The lesion involves the head or neck; this is a close-up image.
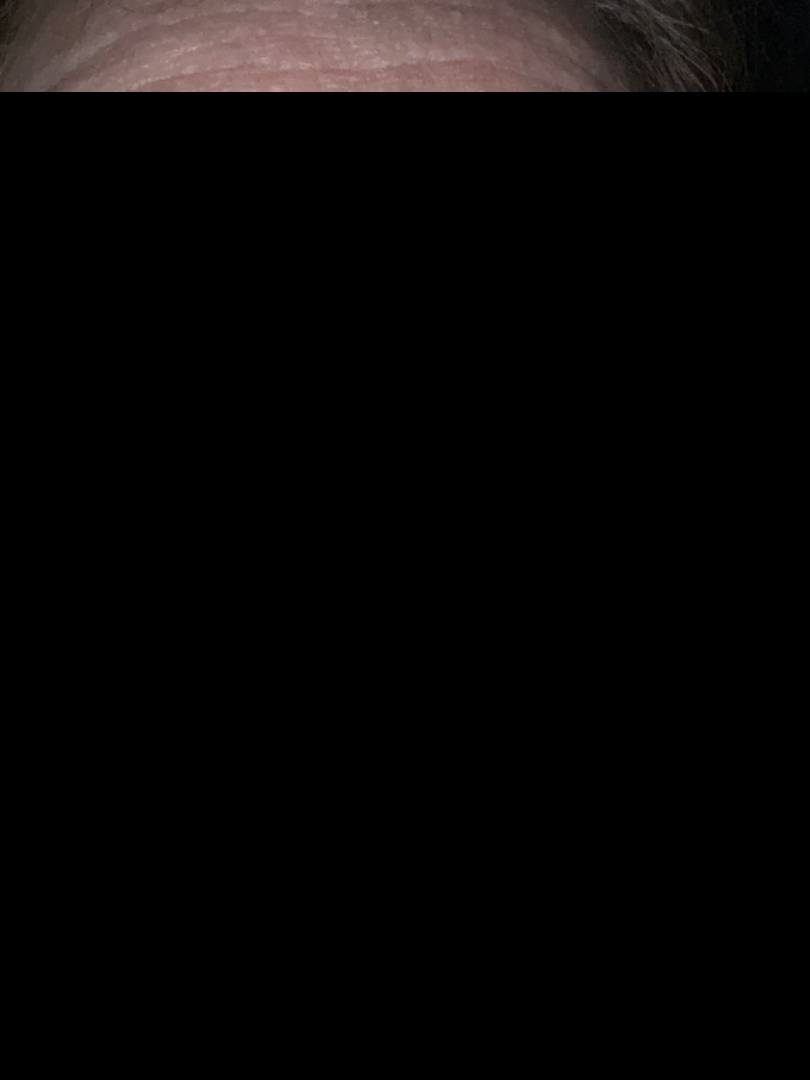* dermatologist impression: Actinic Keratosis (favored)